The subject is a female aged around 50. A dermoscopic close-up of a skin lesion:
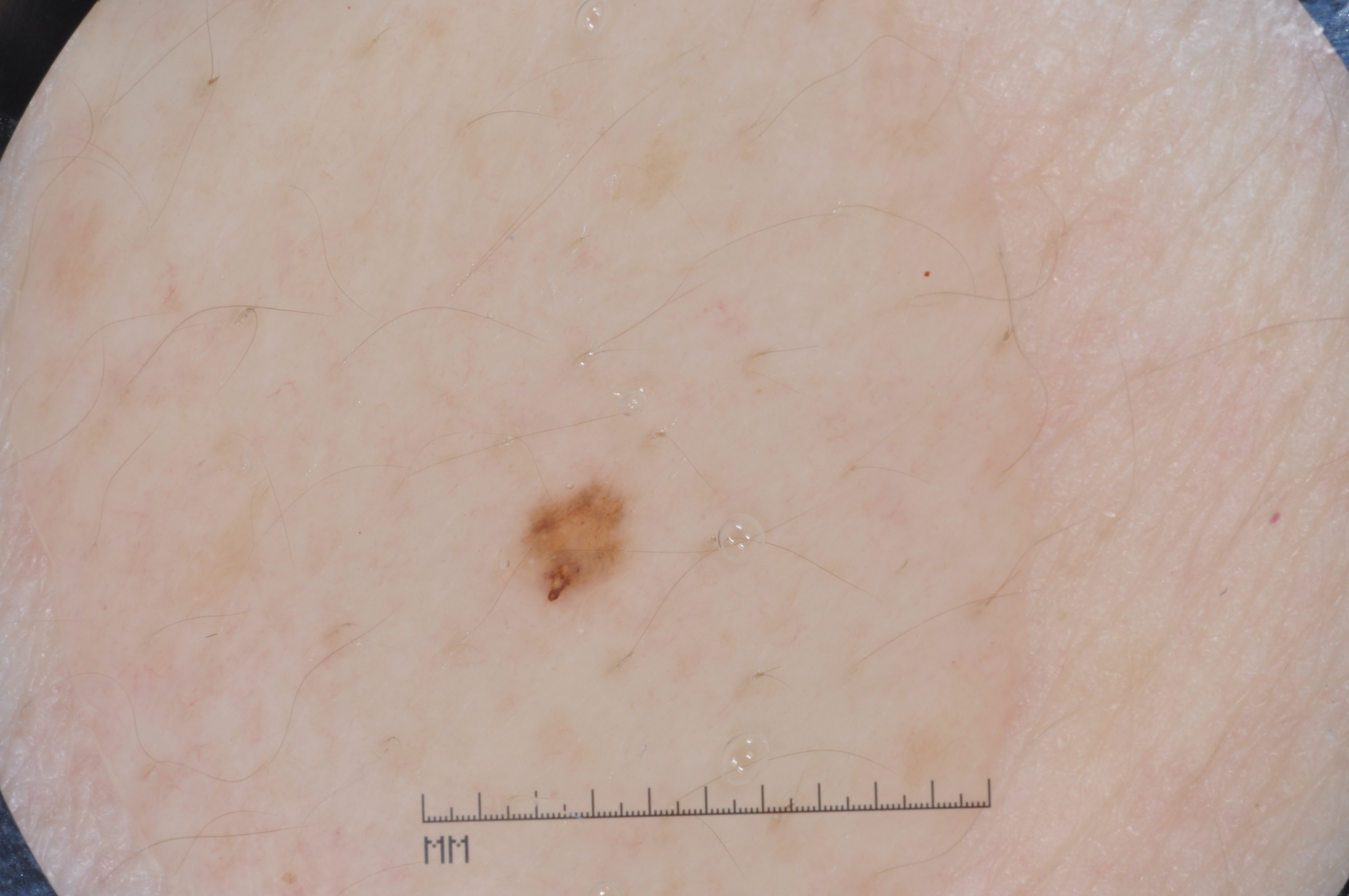Image and clinical context:
As (left, top, right, bottom), the lesion spans box(527, 490, 622, 595). Dermoscopic examination shows milia-like cysts.
Assessment:
Clinically diagnosed as a melanocytic nevus.